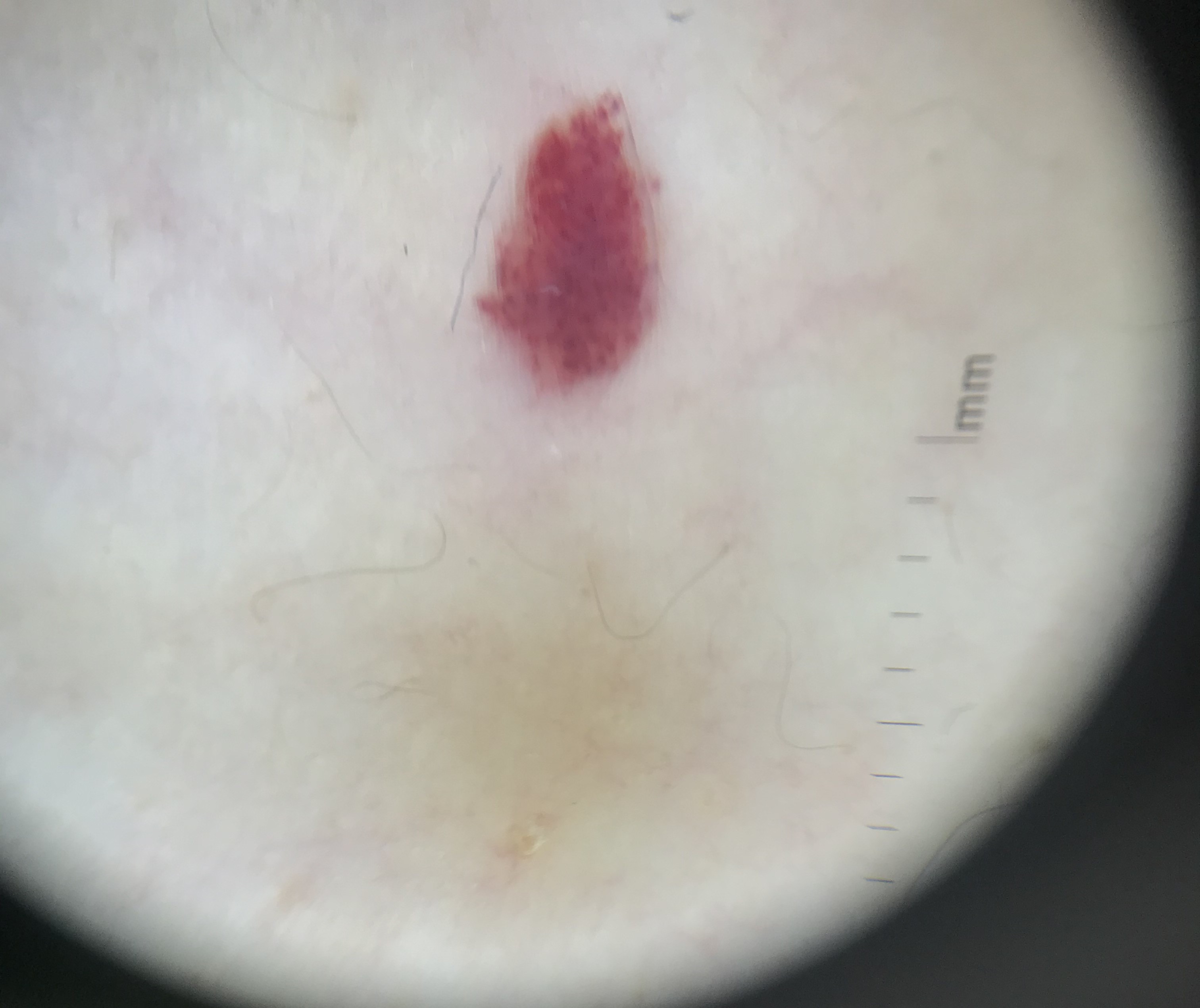A dermoscopic photograph of a skin lesion.
This is a vascular lesion.
Classified as a benign lesion — a hemangioma.